A dermoscopy image of a single skin lesion.
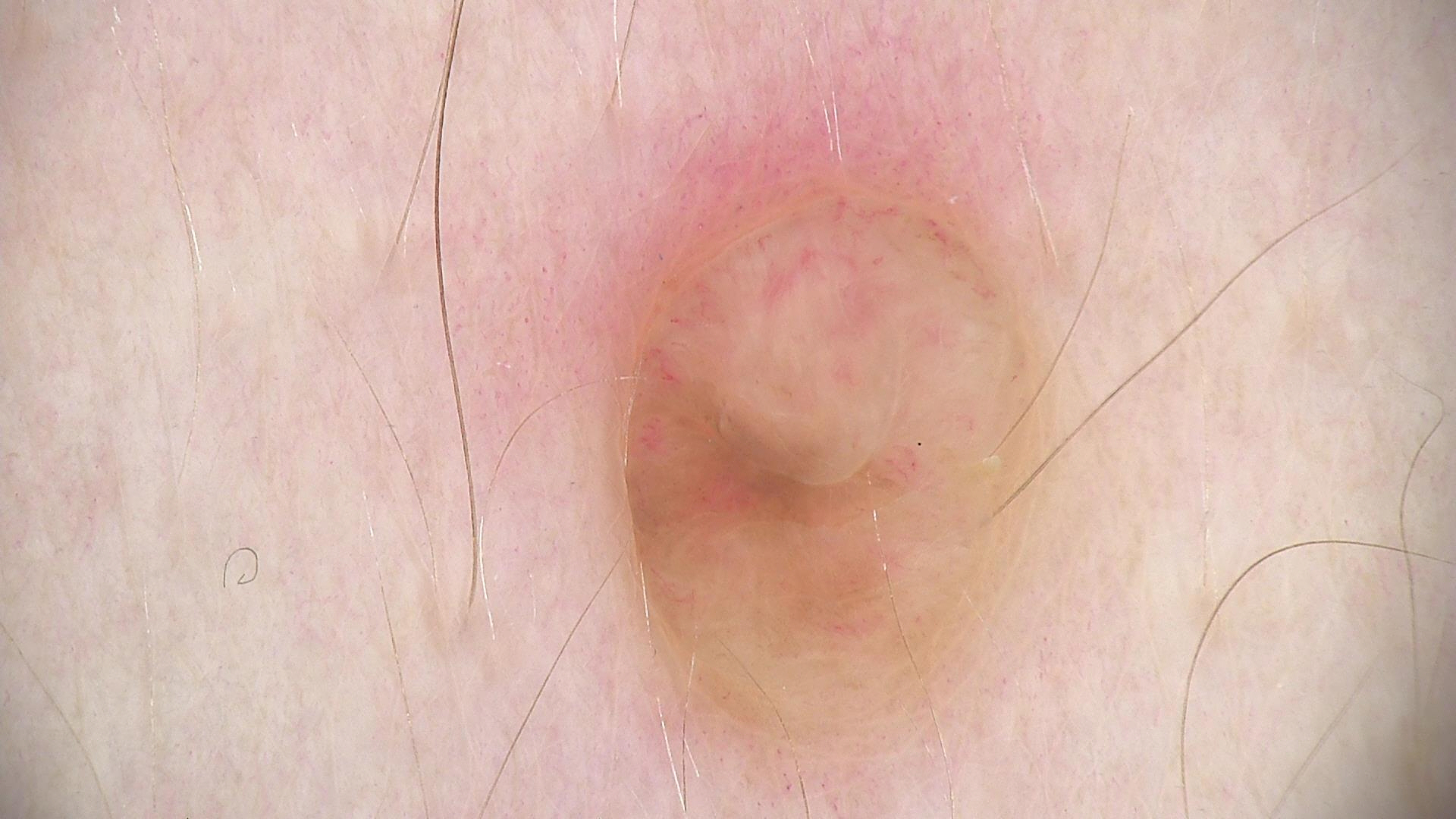Summary: The architecture is that of a banal lesion. Conclusion: The diagnosis was a dermal nevus.